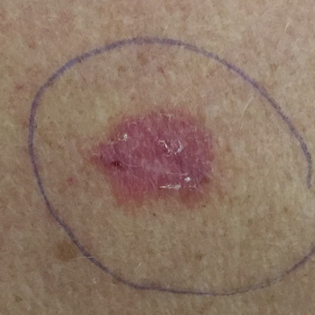Findings: Located on the chest. The patient reports that the lesion has grown, itches, and has changed. Diagnosis: Biopsy-confirmed as a basal cell carcinoma.